A dermoscopic photograph of a skin lesion:
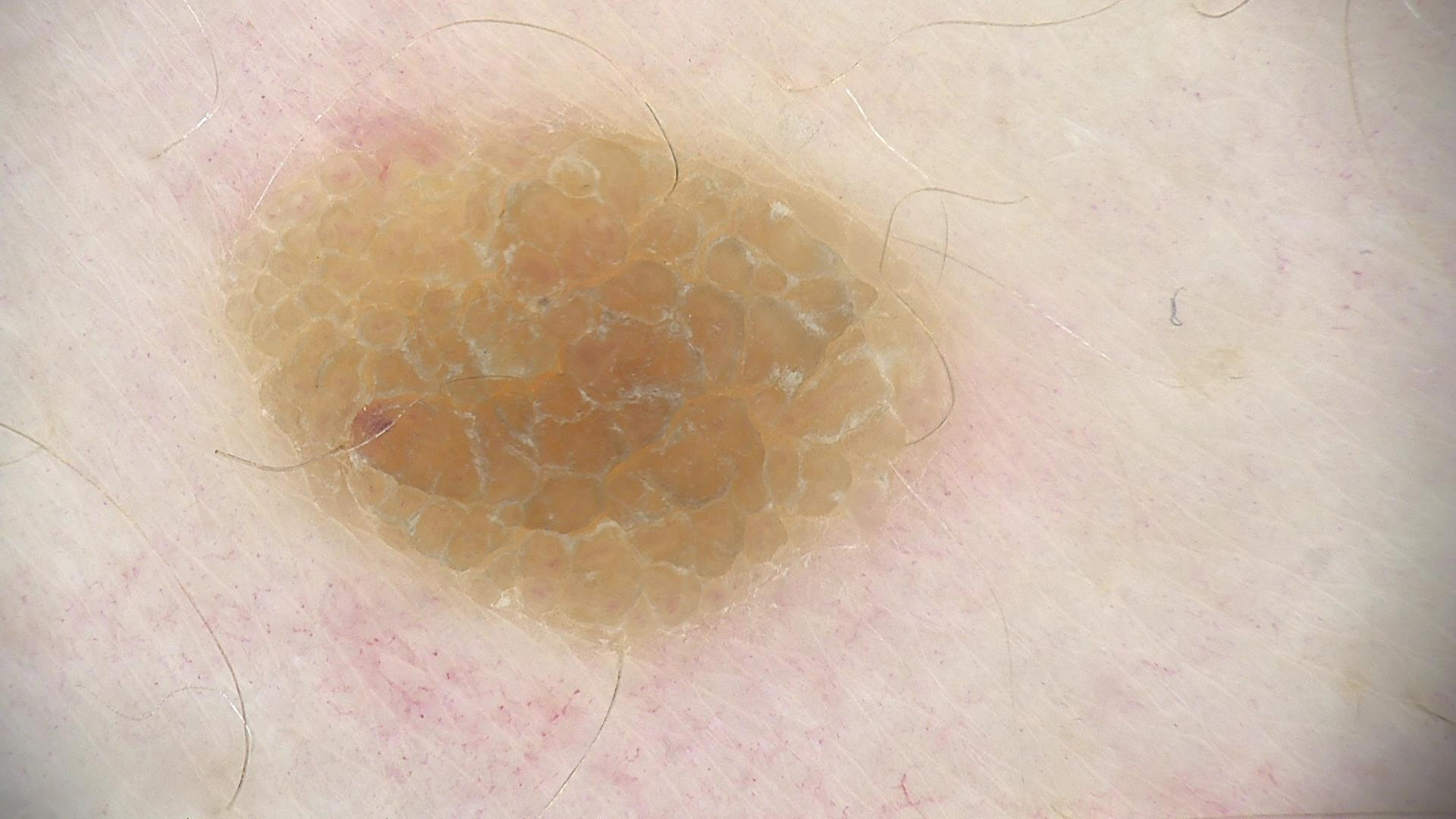lesion type=keratinocytic
diagnostic label=seborrheic keratosis (expert consensus)